Female patient, age 50–59. The lesion involves the top or side of the foot. A close-up photograph — 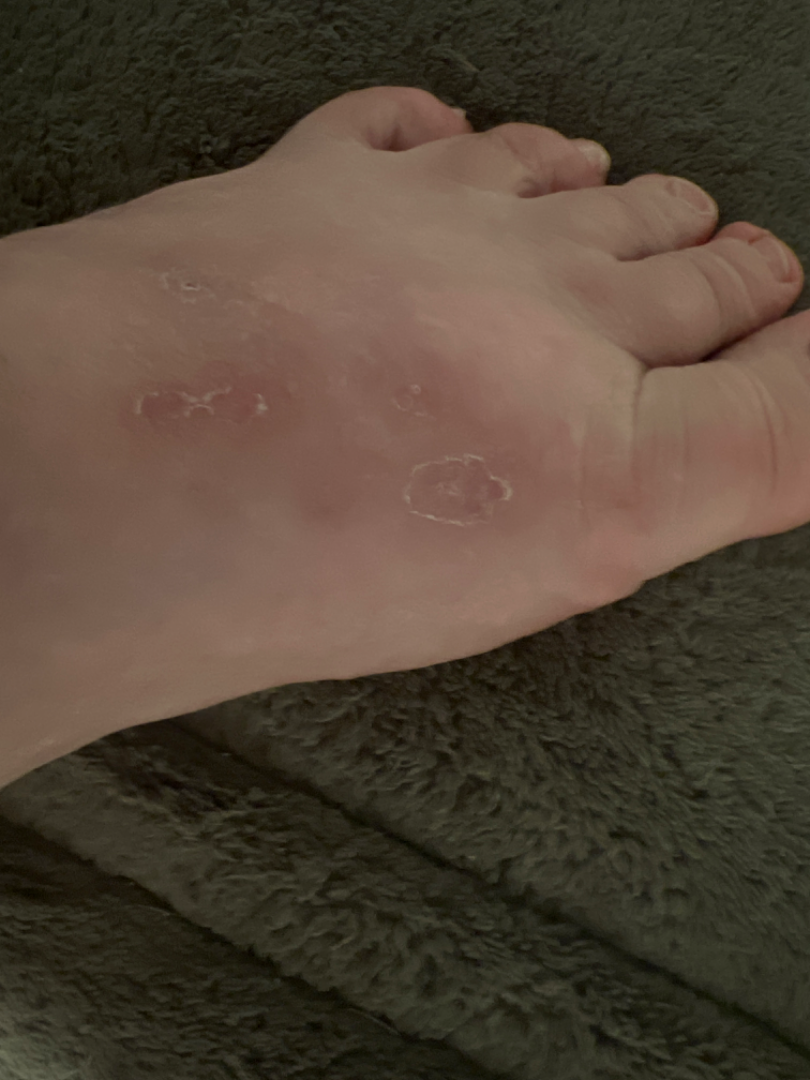Assessment: The skin condition could not be confidently assessed from this image. Clinical context: The patient considered this a rash. The patient indicates itching. The condition has been present for more than one year. The patient indicates the lesion is rough or flaky. No constitutional symptoms were reported.